The contributor reports itching · a close-up photograph · no relevant systemic symptoms · the lesion is described as rough or flaky · the patient described the issue as a rash · the contributor reports the condition has been present for one to three months.
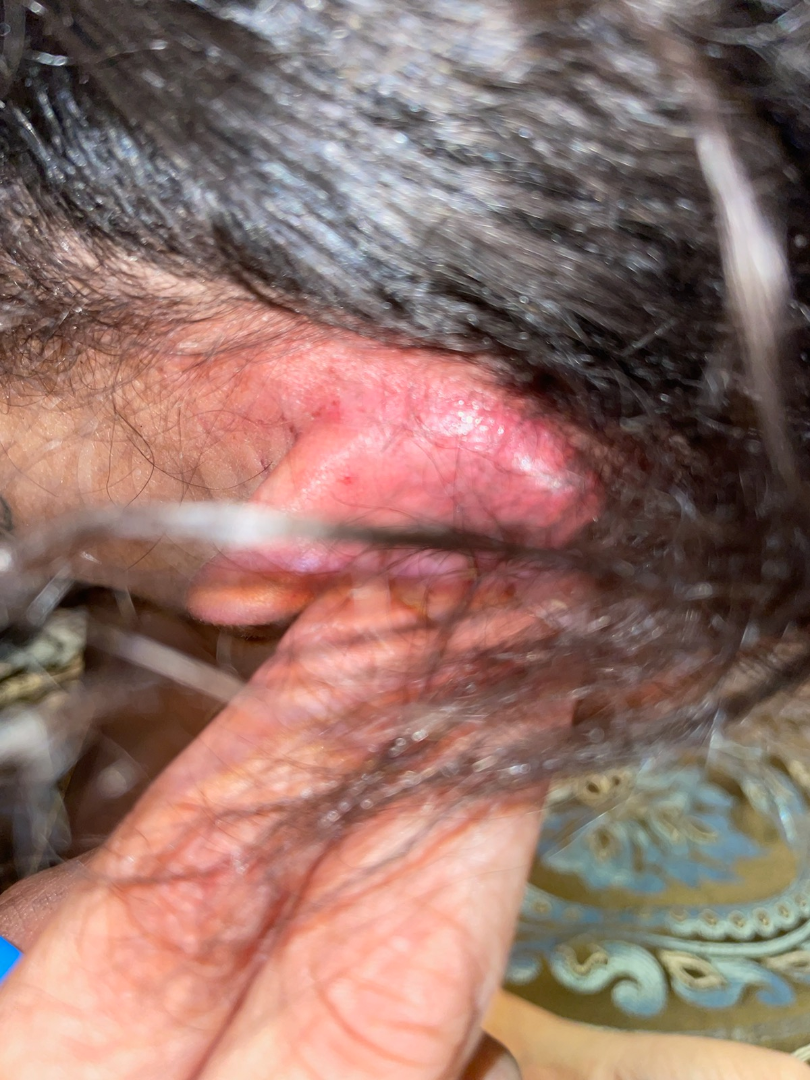<report>
<assessment>could not be assessed</assessment>
</report>